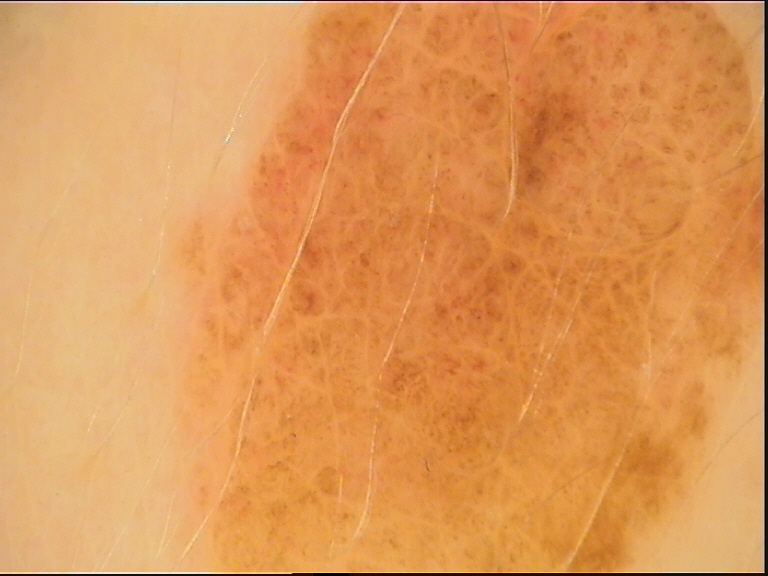Findings:
A dermoscopic image of a skin lesion.
Impression:
The diagnostic label was a compound nevus.